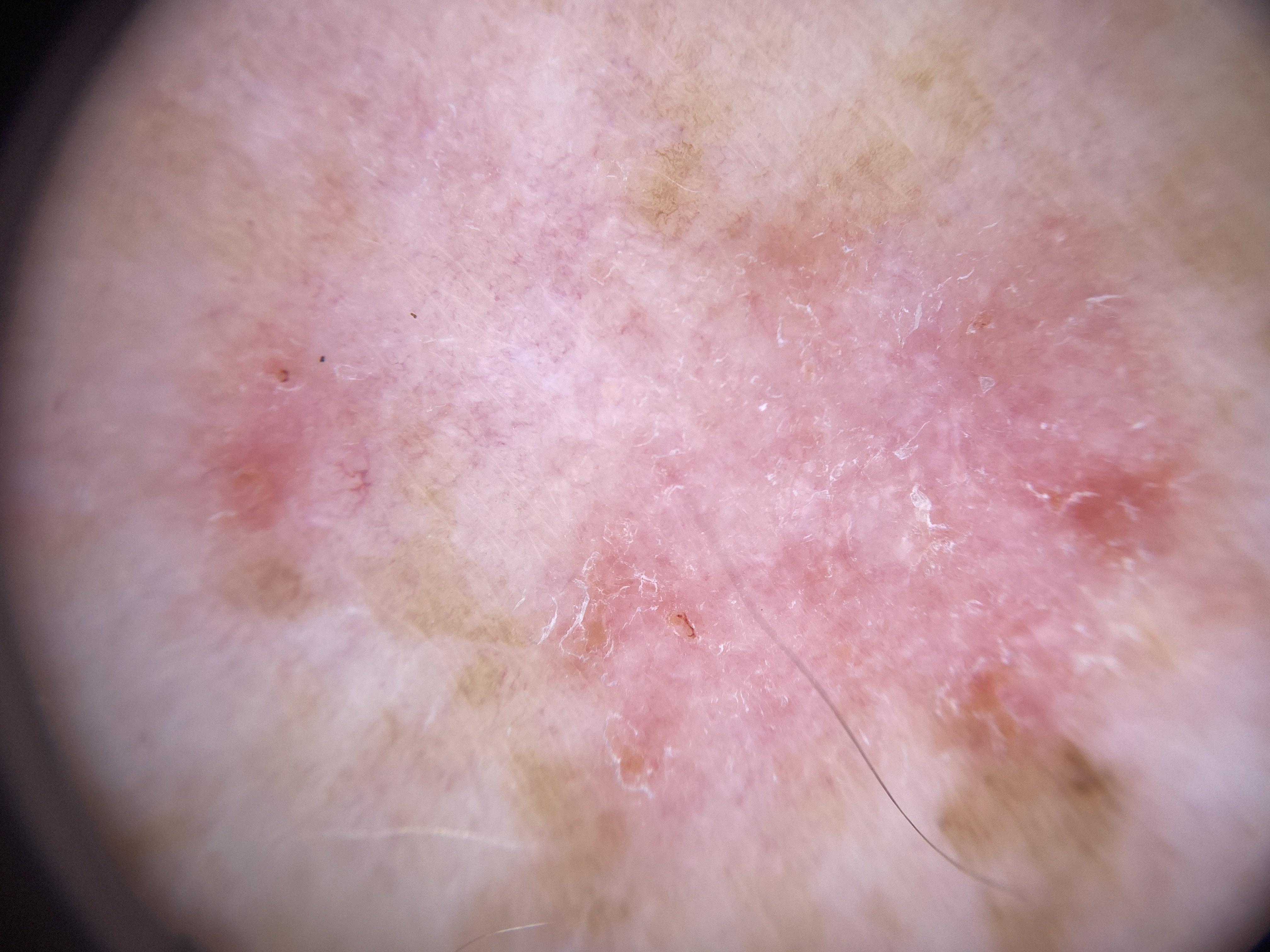image: contact-polarized dermoscopy | location: the posterior trunk | diagnosis: Basal cell carcinoma (biopsy-proven).